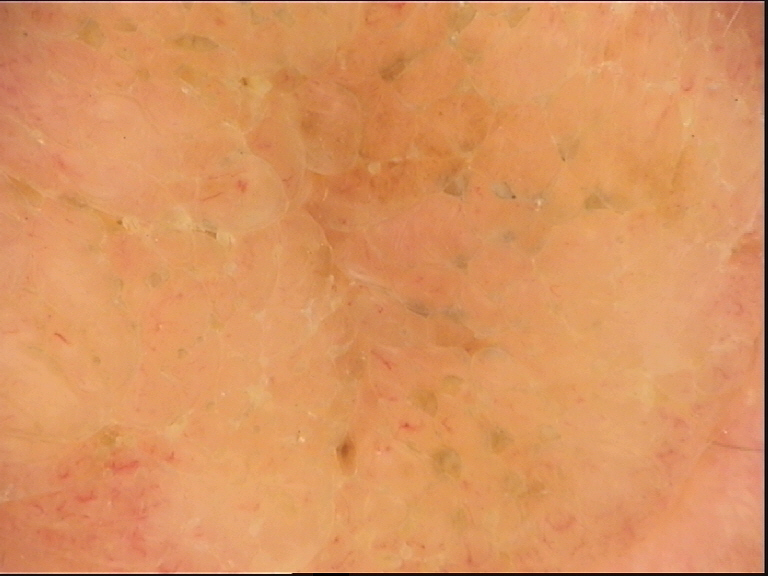A skin lesion imaged with a dermatoscope. The diagnosis was a keratinocytic, benign lesion — a seborrheic keratosis.